The photograph was taken at an angle, the lesion involves the arm and leg, the subject is a female aged 18–29.
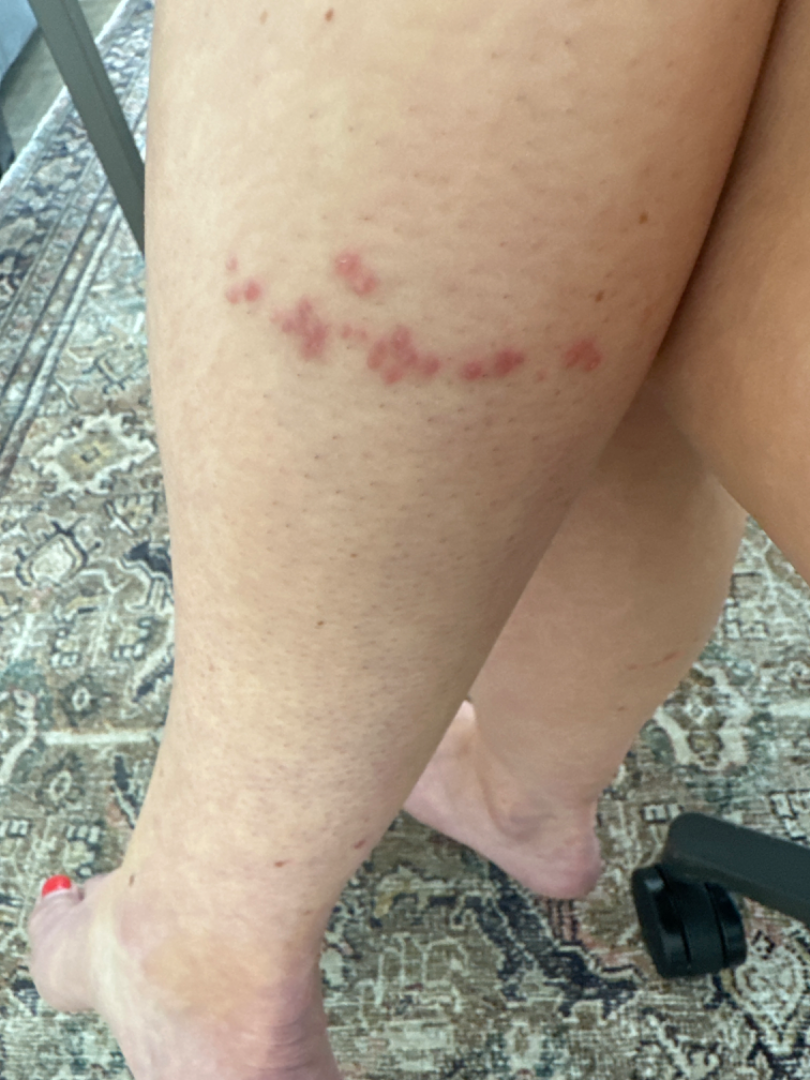The image was not sufficient for the reviewer to characterize the skin condition. The patient considered this a rash. Symptoms reported: bothersome appearance and darkening. The patient notes the condition has been present for less than one week.